The photo was captured at an angle · the patient described the issue as a rash · the lesion is associated with burning · located on the back of the hand, arm and head or neck · the patient also reports joint pain, fatigue and chills · female patient, age 30–39: 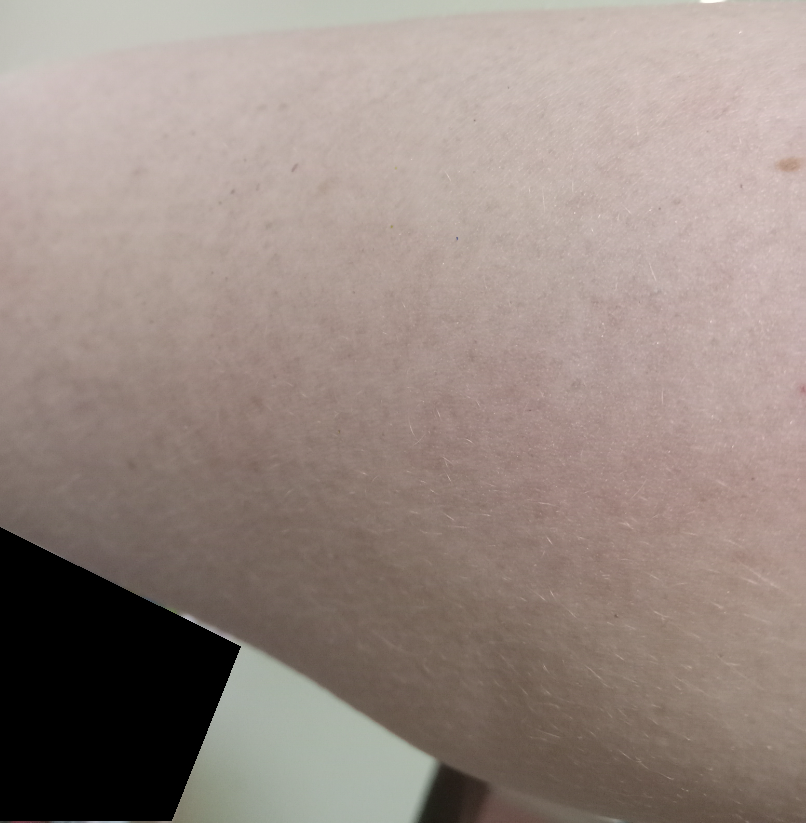The reviewing dermatologist did not identify a discernible skin condition.